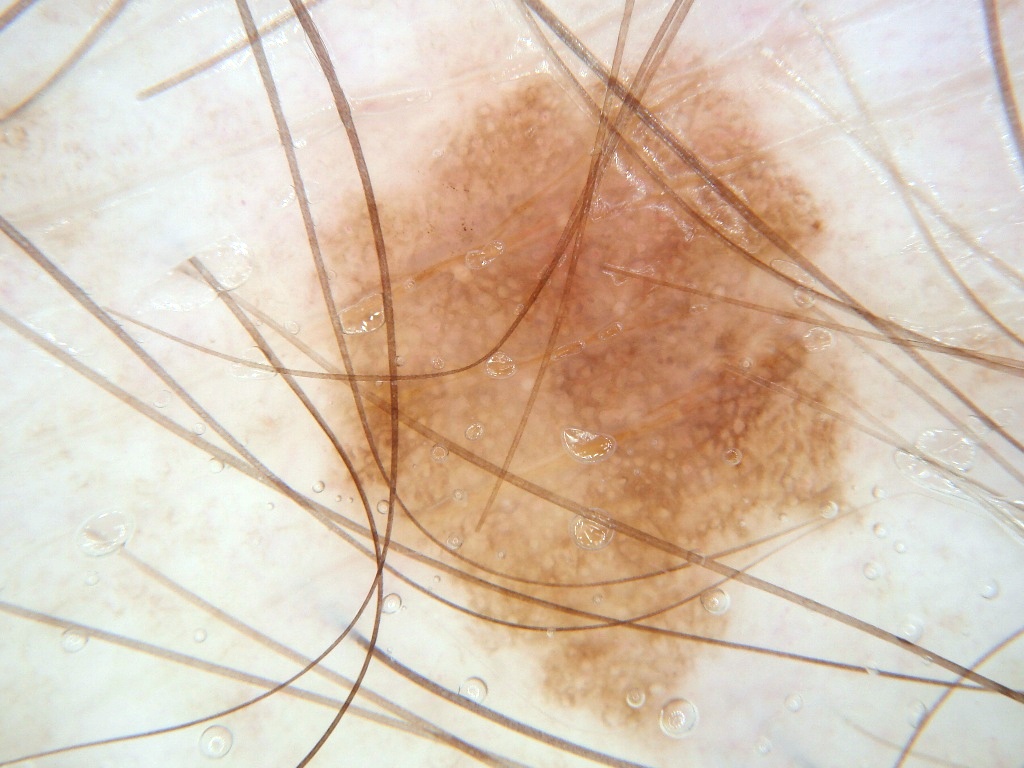Findings: The subject is a male in their 50s. Dermoscopy of a skin lesion. The lesion is bounded by x1=283, y1=35, x2=886, y2=764. The lesion takes up about 40% of the image. Dermoscopic review identifies globules and pigment network, with no negative network, milia-like cysts, or streaks. Impression: Expert review diagnosed this as a melanocytic nevus.